The chart notes pesticide exposure, tobacco use, no alcohol use, and no prior skin cancer (patient or family); a female subject in their 50s; Fitzpatrick phototype III — 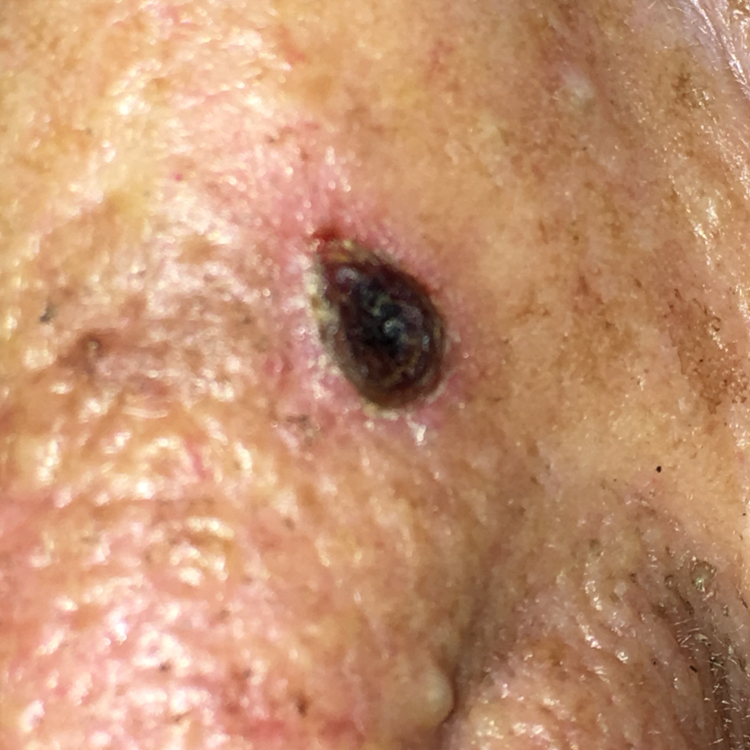The lesion measures 3 × 2 mm.
Per patient report, the lesion has grown, is elevated, and has bled.
Histopathology confirmed a basal cell carcinoma.